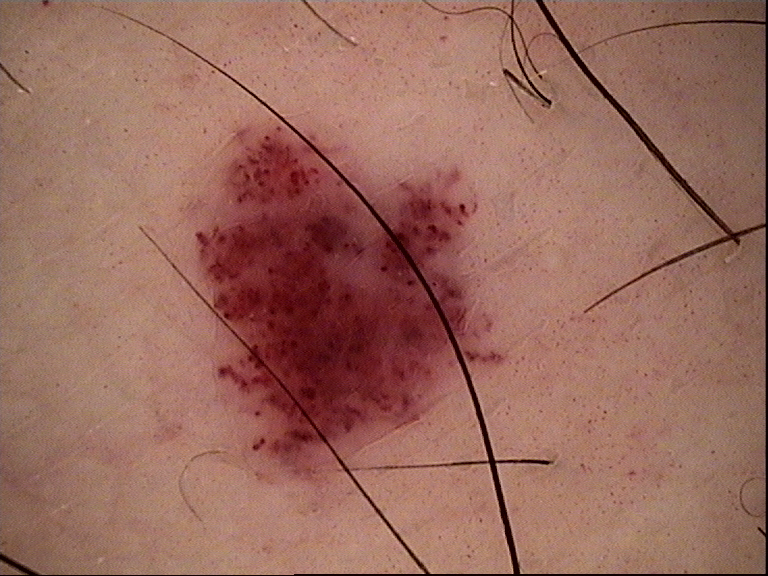assessment = hemangioma (expert consensus).